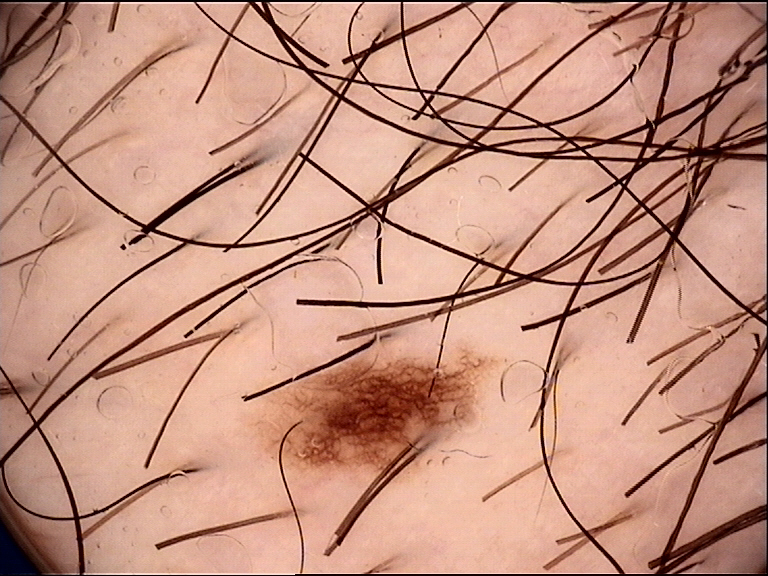Diagnosed as a dysplastic junctional nevus.